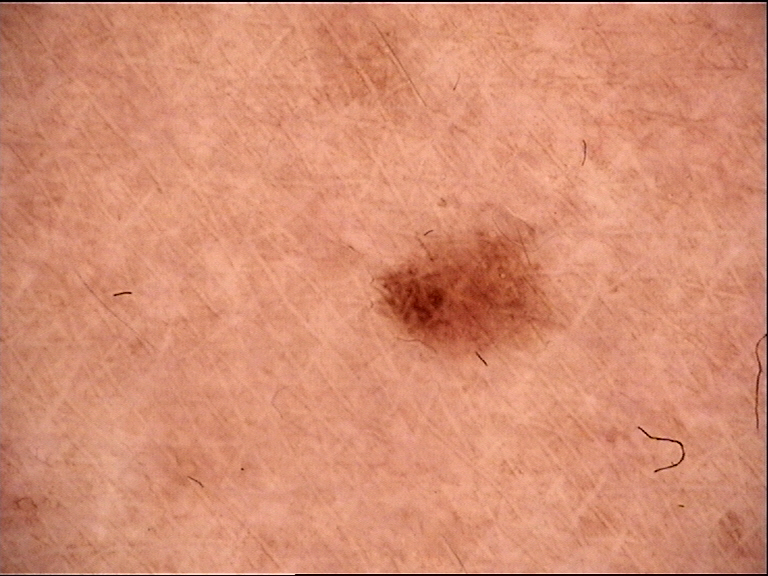assessment = dysplastic junctional nevus (expert consensus).